The affected area is the leg, head or neck and arm; the photo was captured at an angle; female contributor, age 70–79:
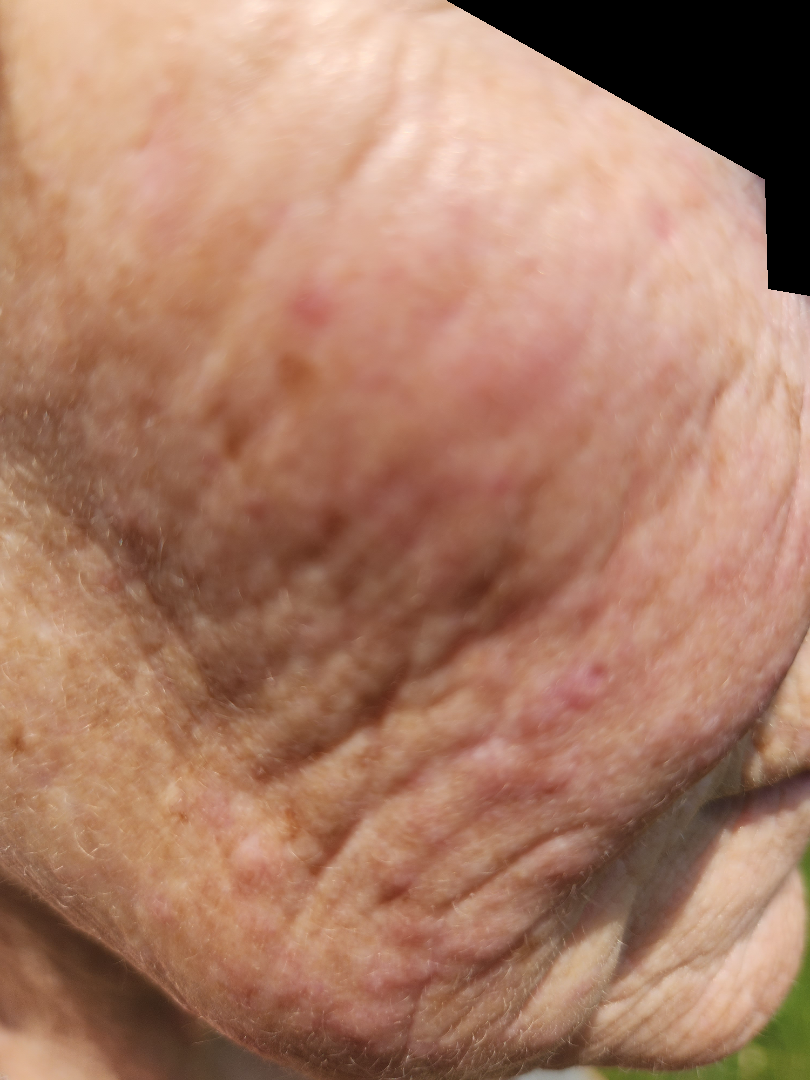Findings: The skin condition could not be confidently assessed from this image. Background: Fitzpatrick skin type III; human graders estimated Monk skin tone scale 2–3. The patient considered this a rash. Reported duration is less than one week. No associated lesion symptoms were reported.